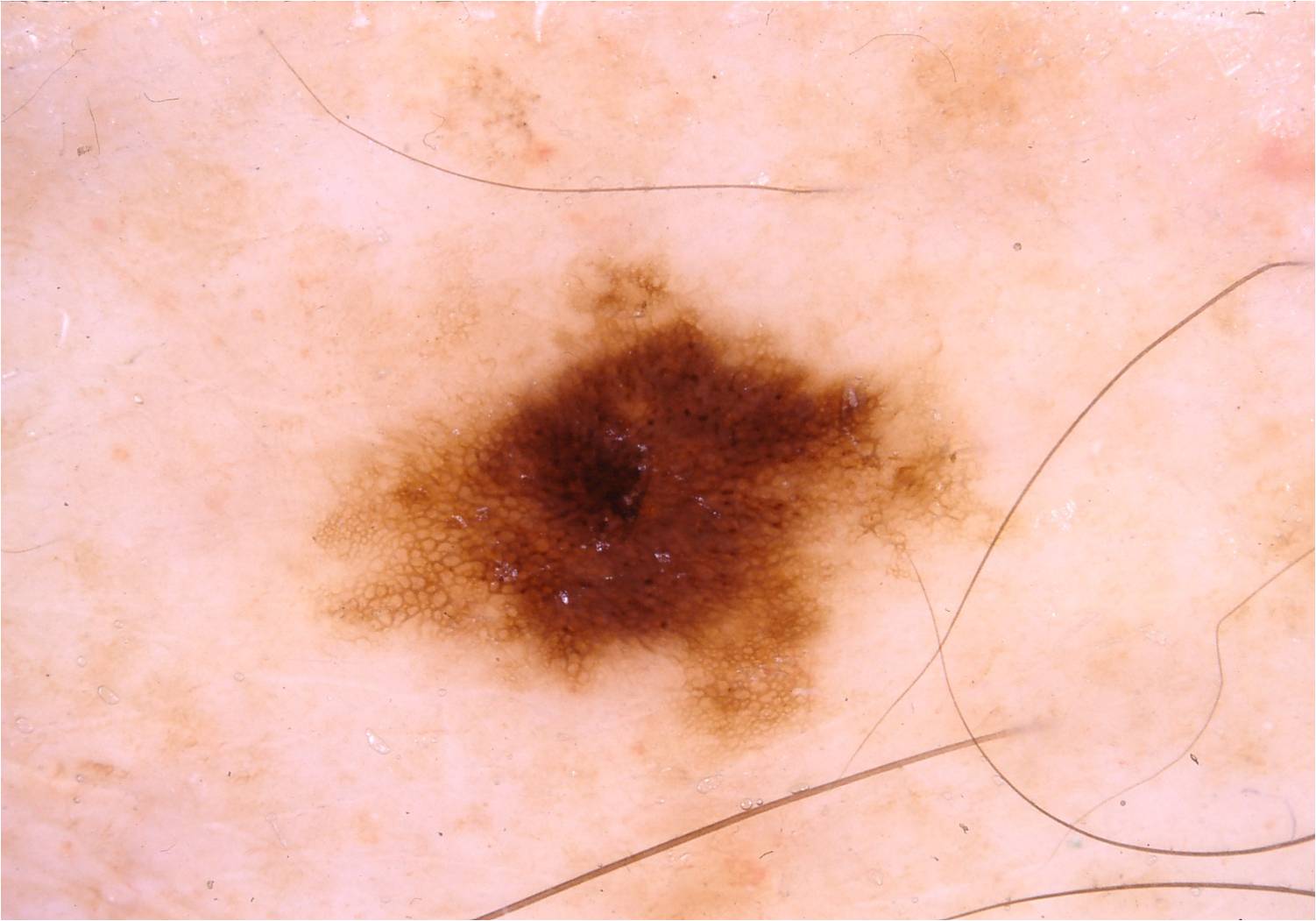  image:
    modality: dermoscopy
  patient:
    sex: female
    age_approx: 80
  lesion_location:
    bbox_xyxy:
      - 315
      - 240
      - 968
      - 760
  dermoscopic_features:
    present:
      - pigment network
      - globules
    absent:
      - streaks
      - milia-like cysts
      - negative network
  diagnosis:
    name: melanocytic nevus
    malignancy: benign
    lineage: melanocytic
    provenance: clinical